The top or side of the foot is involved. The photograph is a close-up of the affected area:
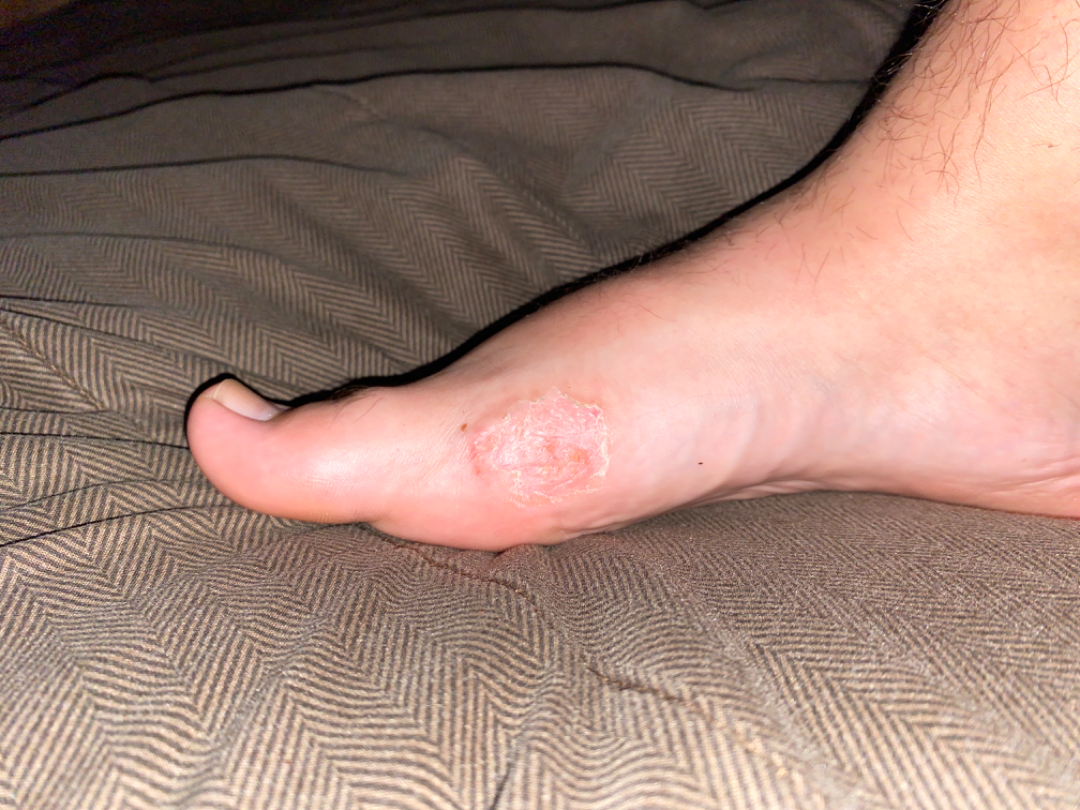assessment=could not be assessed